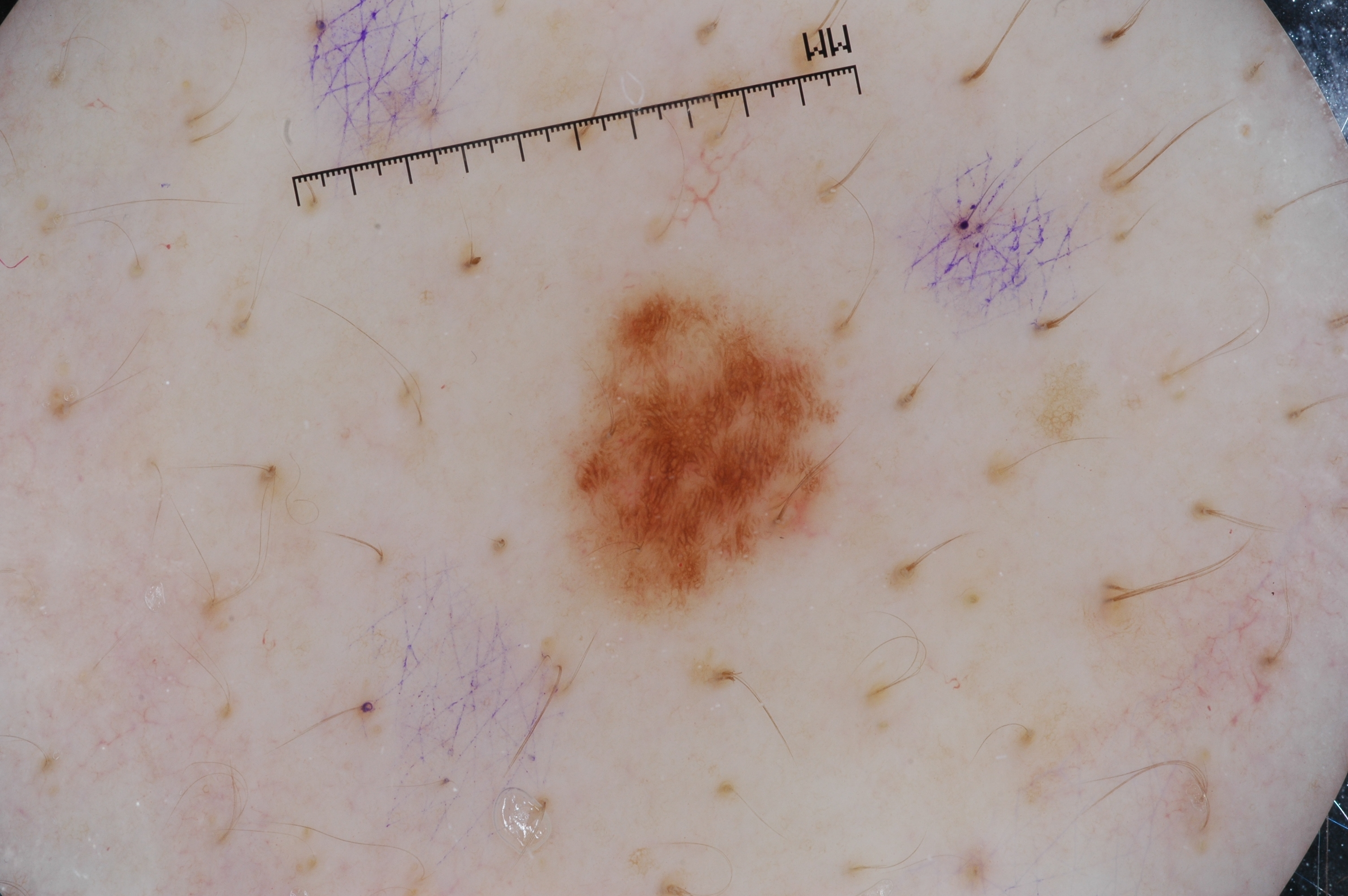The patient is a male in their mid- to late 40s.
A dermoscopic image of a skin lesion.
On dermoscopy, the lesion shows pigment network and milia-like cysts.
In (x1, y1, x2, y2) order, the lesion's extent is (553, 273, 844, 625).
The lesion covers approximately 6% of the dermoscopic field.
Diagnosed as a melanocytic nevus.